Located on the front of the torso, arm, back of the torso and leg · an image taken at an angle · the patient considered this a rash · texture is reported as raised or bumpy · the contributor notes the condition has been present for less than one week · the lesion is associated with burning, enlargement and itching — 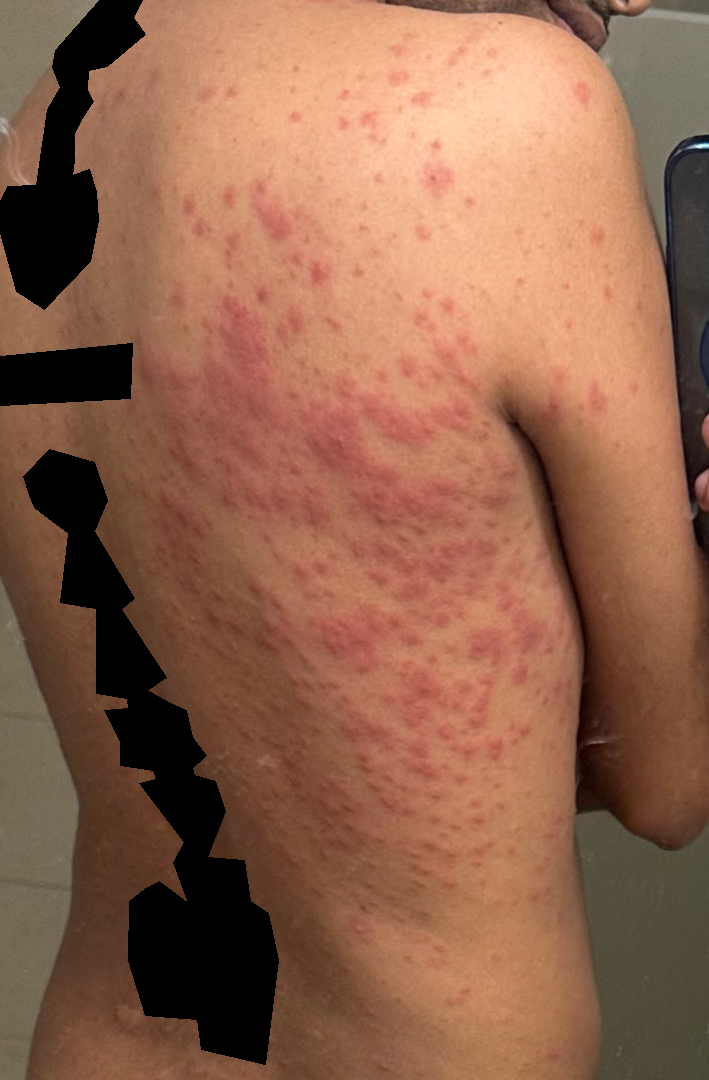Impression:
Three dermatologists each reviewed the case: most likely Drug Rash; a remote consideration is Viral Exanthem; lower on the differential is Scabies; less likely is Folliculitis; less probable is Allergic Contact Dermatitis.